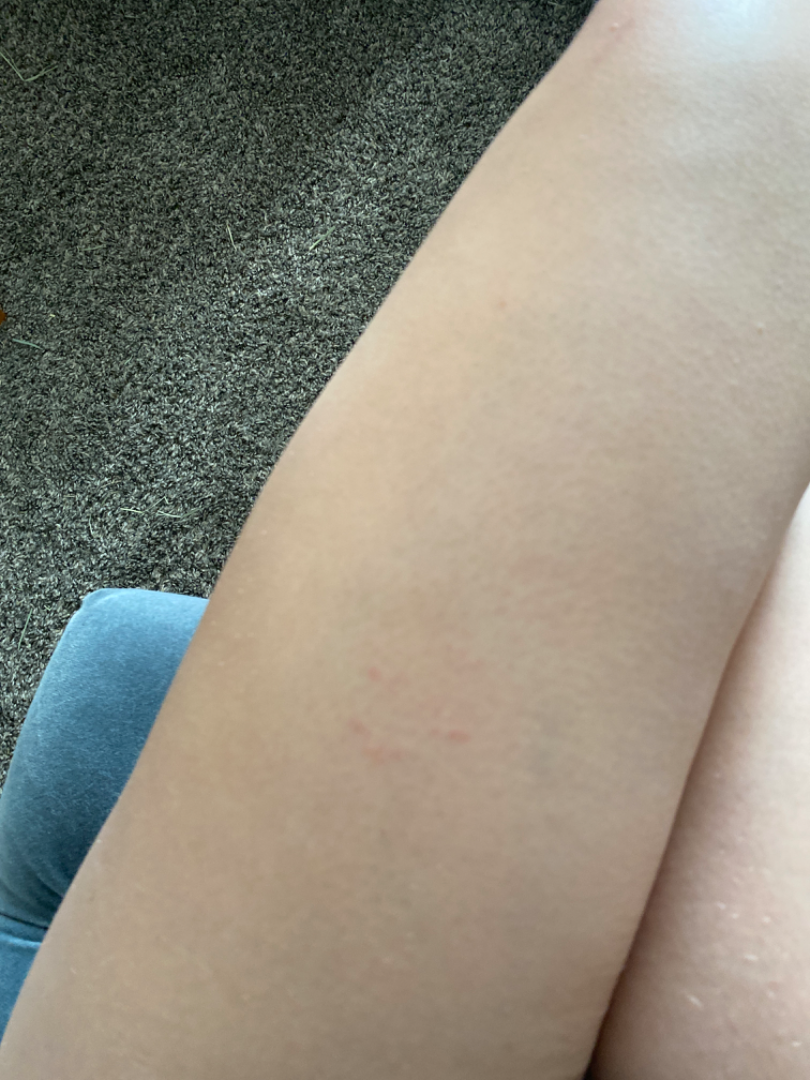Q: Could the case be diagnosed?
A: indeterminate